The patient is FST II; a male patient aged approximately 75.
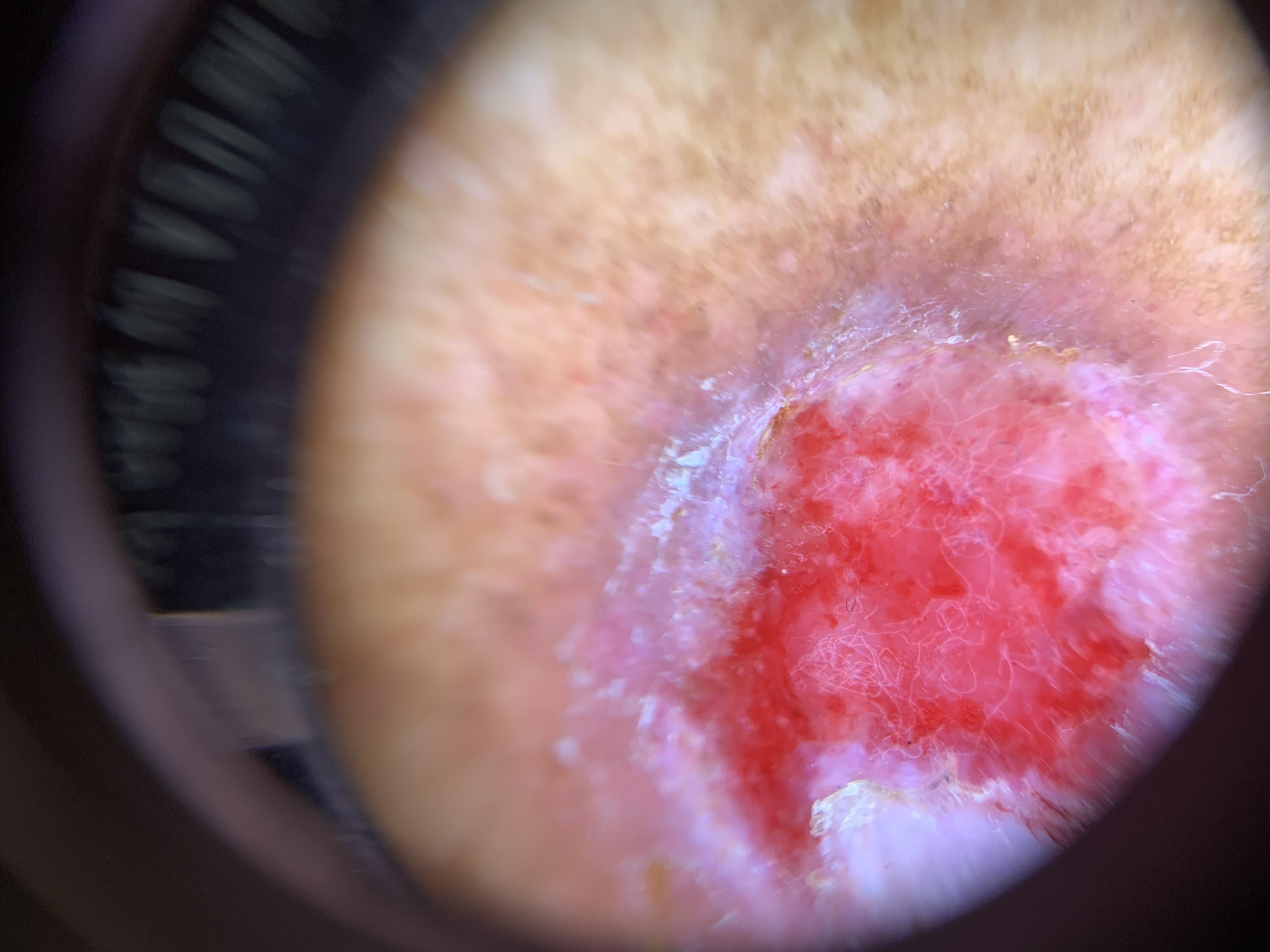Clinical context:
The lesion is on a lower extremity.
Diagnosis:
Histopathological examination showed a skin cancer — a basal cell carcinoma.